A dermoscopy image of a skin lesion · a male subject 60 years old · referred with a clinical suspicion of basal cell carcinoma: 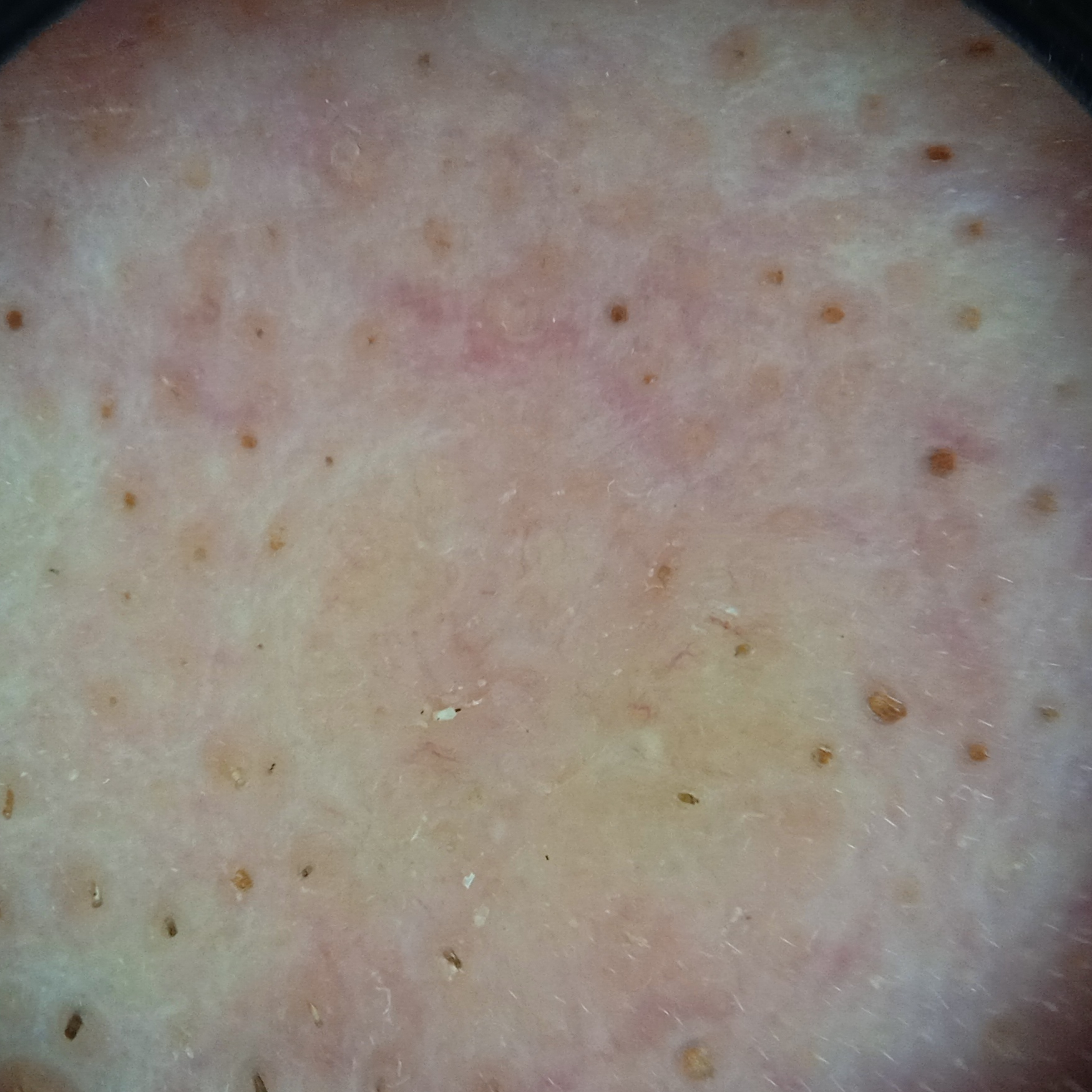Located on the face. The lesion measures approximately 8.5 mm. The biopsy diagnosis was a basal cell carcinoma, following excision, with a measured tumor thickness of 1.7 mm.